The photo was captured at a distance. Present for less than one week. No associated systemic symptoms reported. The patient described the issue as skin that appeared healthy to them. Texture is reported as raised or bumpy. The affected area is the back of the hand. The patient notes itching — 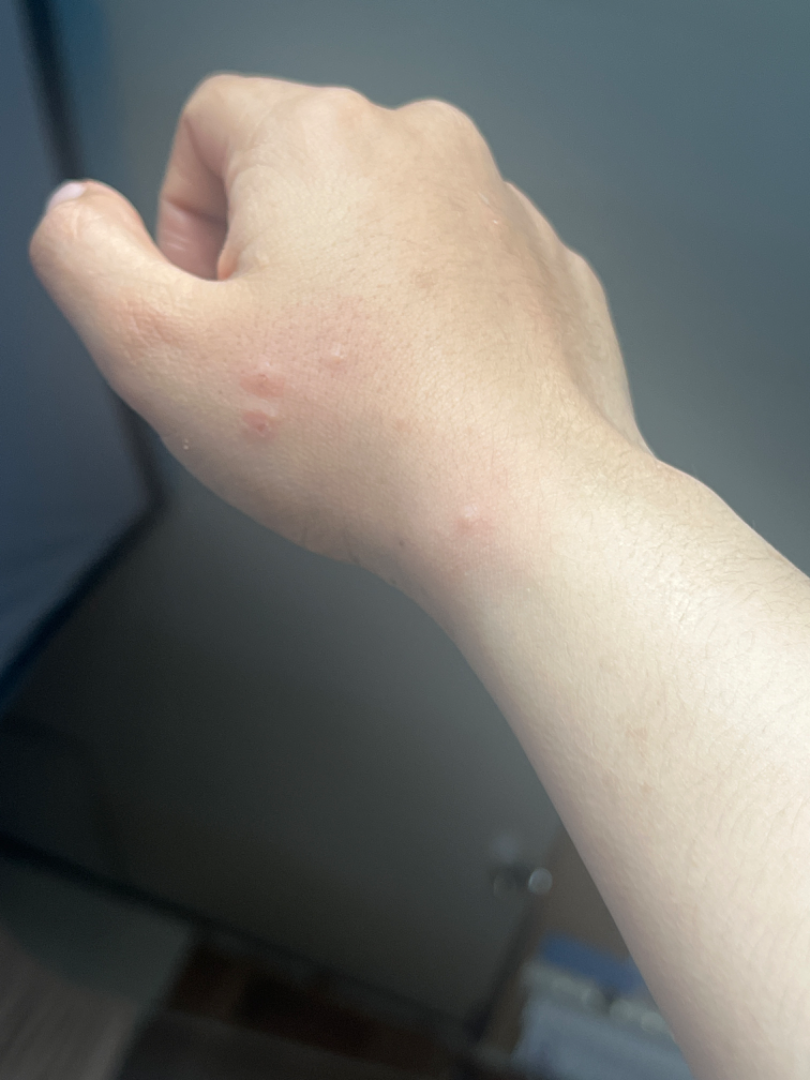<dermatology_case>
  <differential>Urticaria, Insect Bite</differential>
</dermatology_case>